This is a close-up image — 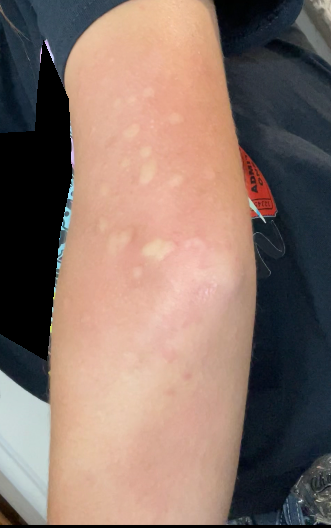Findings: On photographic review by a dermatologist: Urticaria (1.00).